The subject is a male aged 63-67, a dermoscopic close-up of a skin lesion: 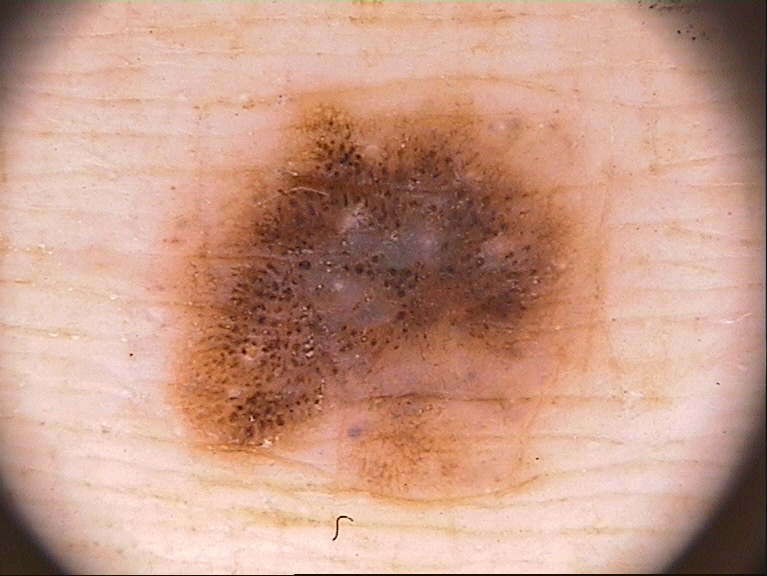dermoscopic pattern — globules and pigment network | lesion location — 146, 81, 617, 508 | size — ~38% of the field | impression — a melanocytic nevus, a benign skin lesion.